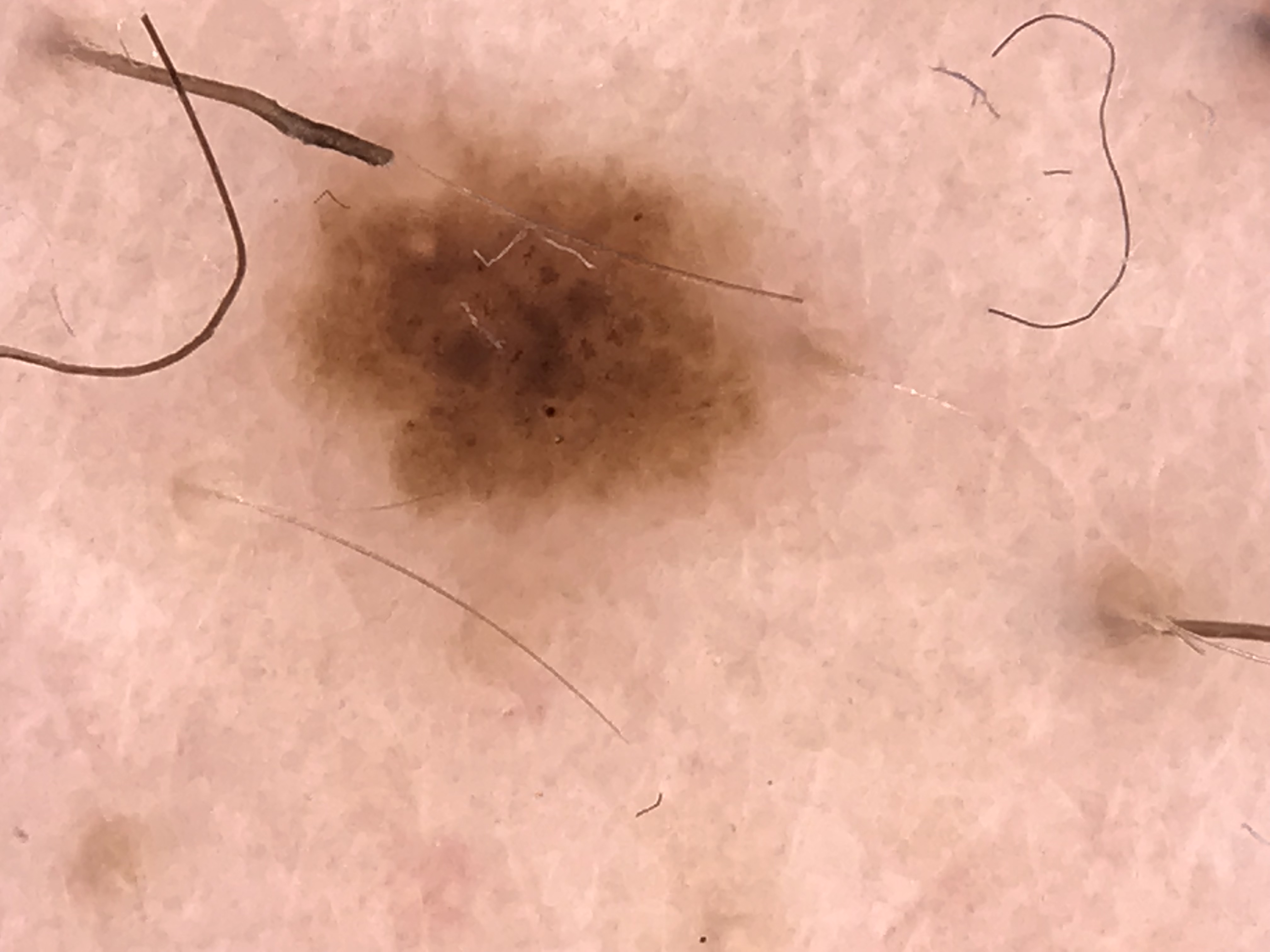Conclusion:
Consistent with a dysplastic junctional nevus.